The patient reports a personal history of skin cancer, a personal history of cancer, and no immunosuppression · the patient says their skin tans without first burning · collected as part of a research study, without a referral diagnosis · the patient describes having a moderate number of moles · a dermatoscopic image of a skin lesion · a female patient 75 years old — 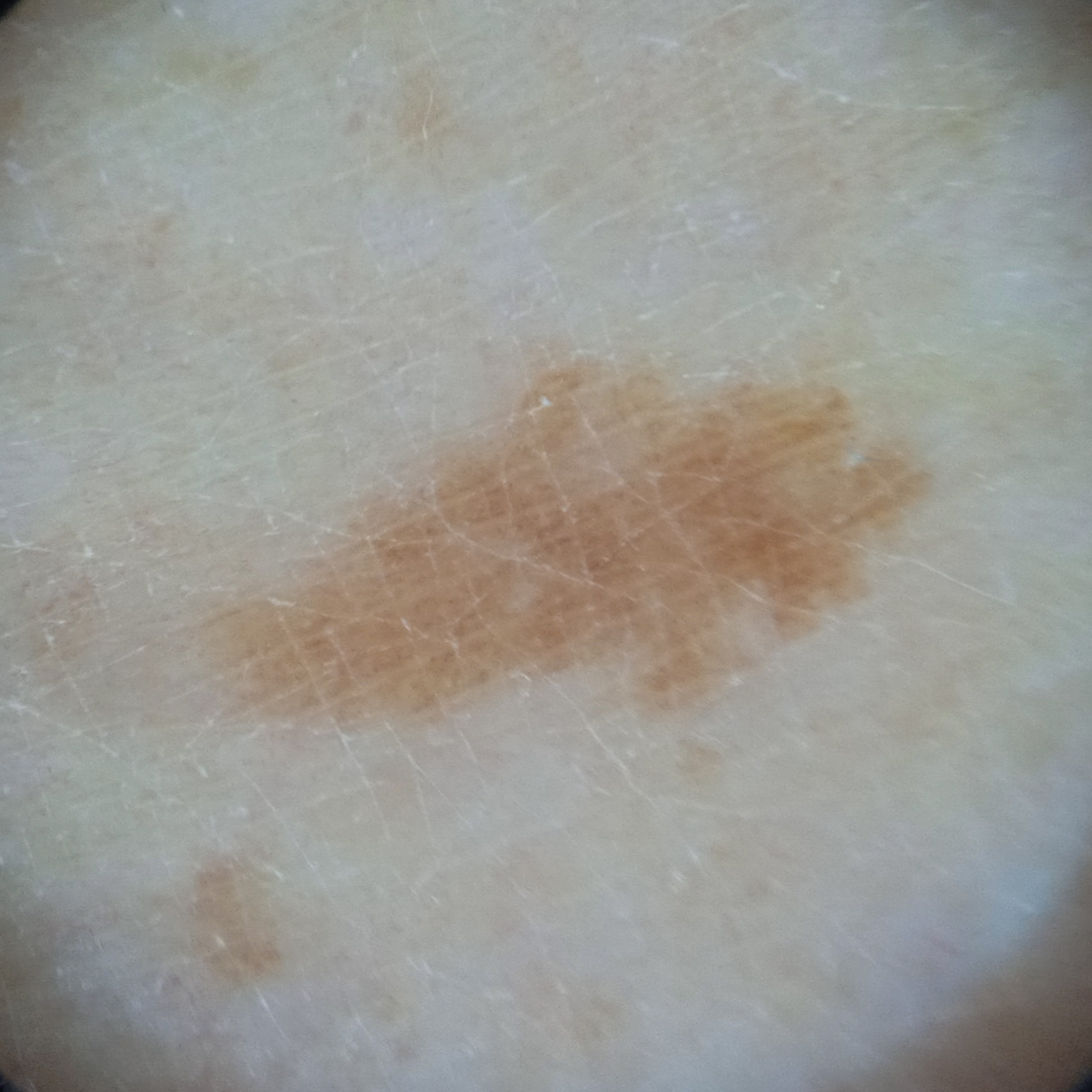The lesion involves a leg.
The lesion is about 8.2 mm across.
The dermatologists' assessment was a melanocytic nevus.